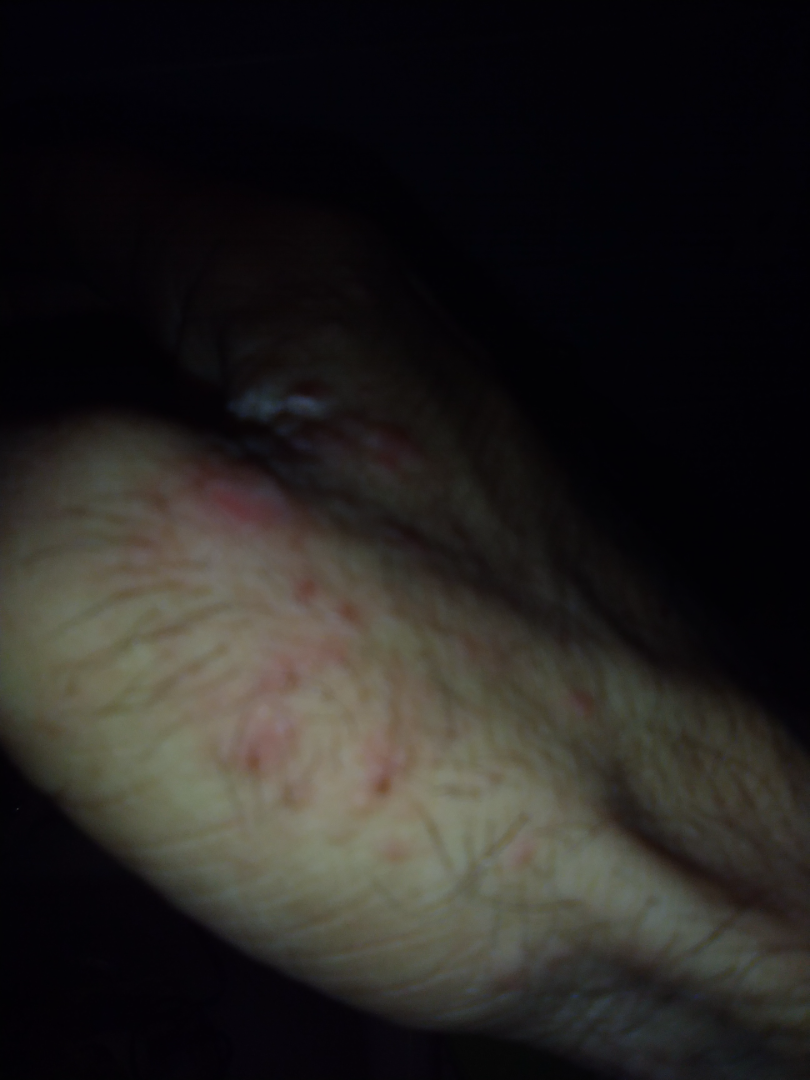Notes:
- assessment · unable to determine
- shot type · at an angle
- other reported symptoms · none reported
- skin tone · non-clinician graders estimated Monk Skin Tone 4
- body site · head or neck, front of the torso and arm